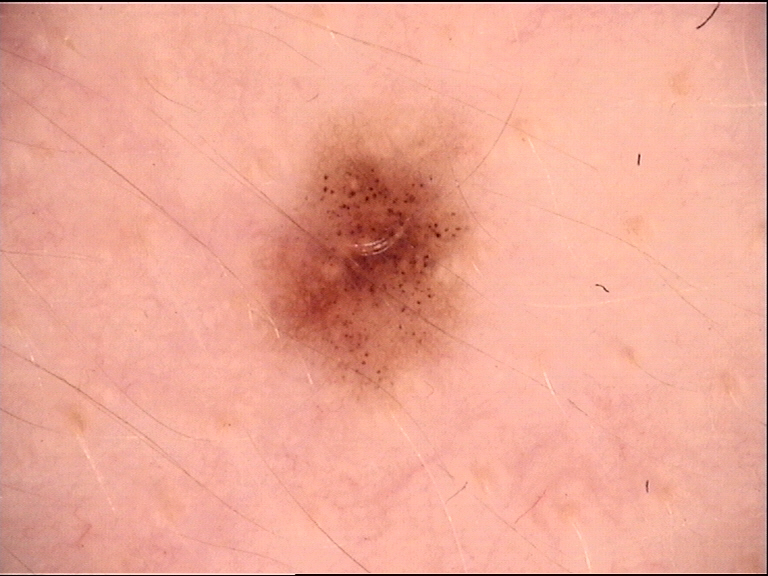Dermoscopy of a skin lesion.
Classified as a benign lesion — a dysplastic junctional nevus.